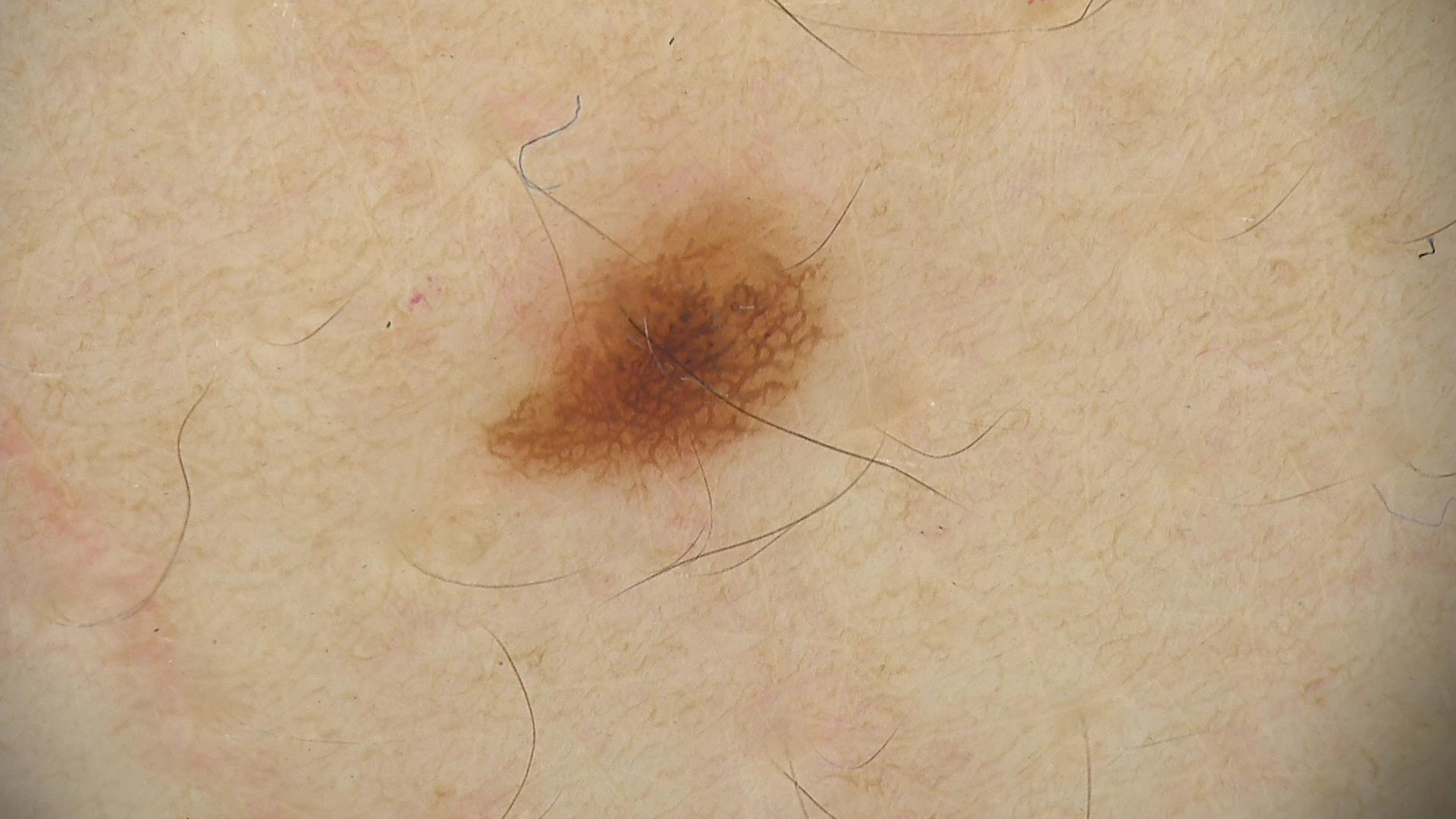Findings:
- image type: dermatoscopy
- class: dysplastic junctional nevus (expert consensus)